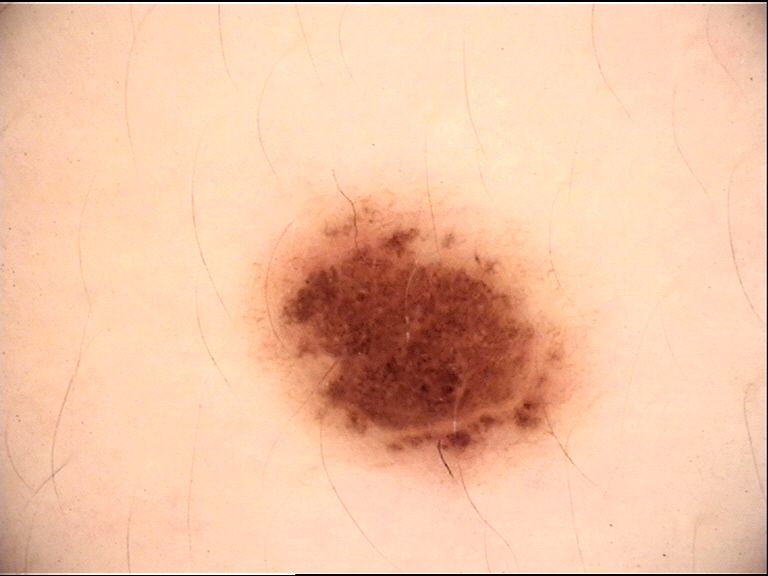Findings:
– subtype: banal
– diagnosis: compound nevus (expert consensus)